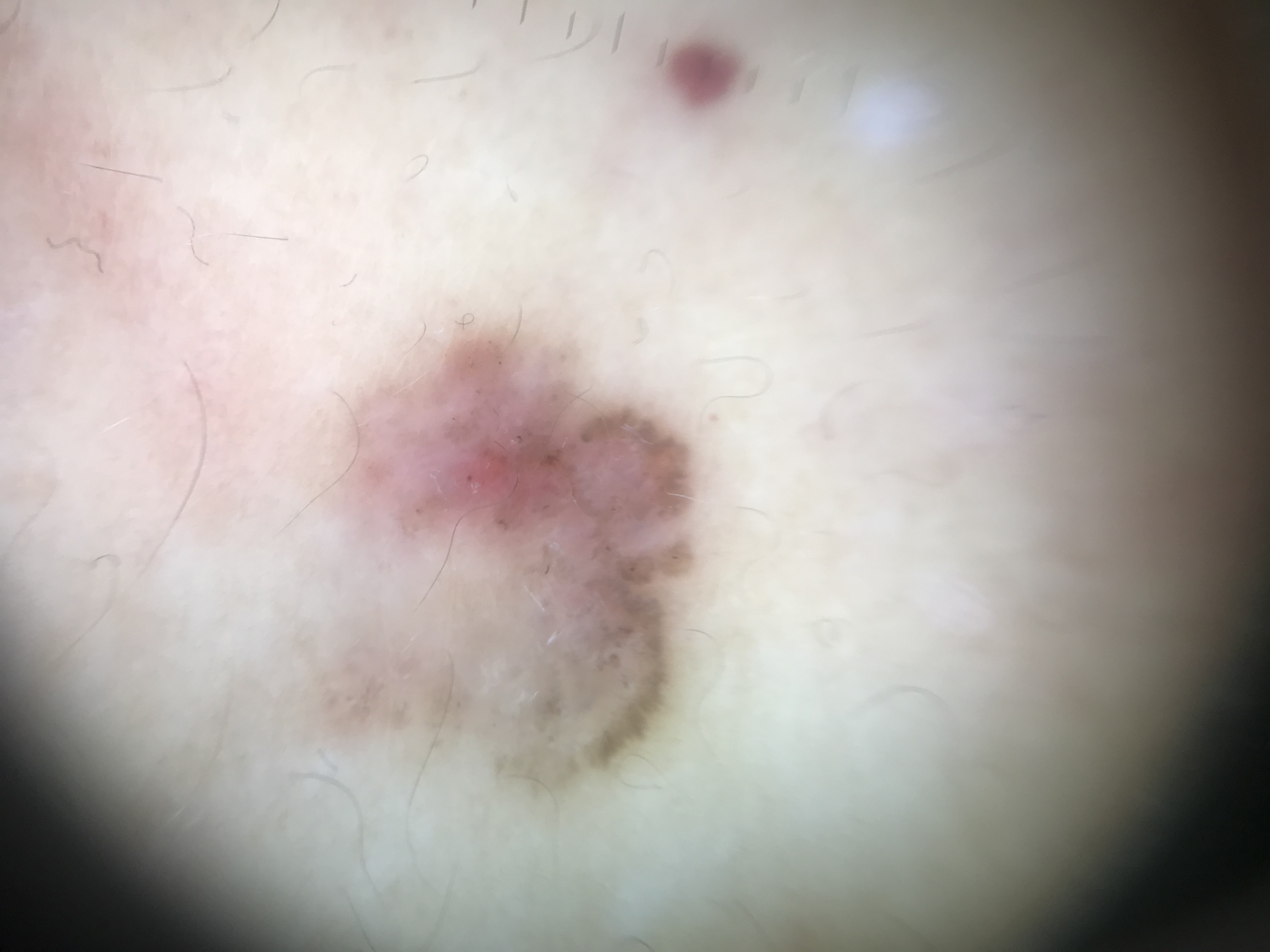Case:
A skin lesion imaged with a dermatoscope.
Pathology:
Biopsy-confirmed as a malignant, keratinocytic lesion — a basal cell carcinoma.